A dermatoscopic image of a skin lesion.
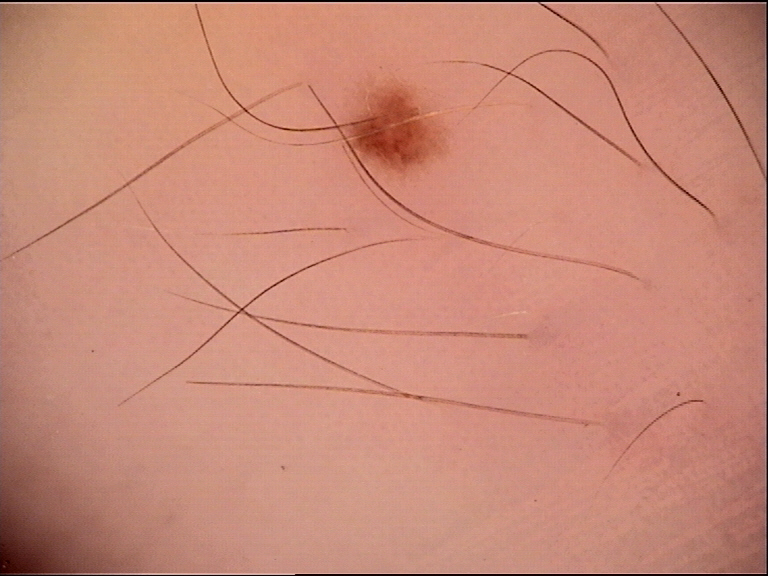Case:
The architecture is that of a banal lesion.
Impression:
Consistent with a junctional nevus.